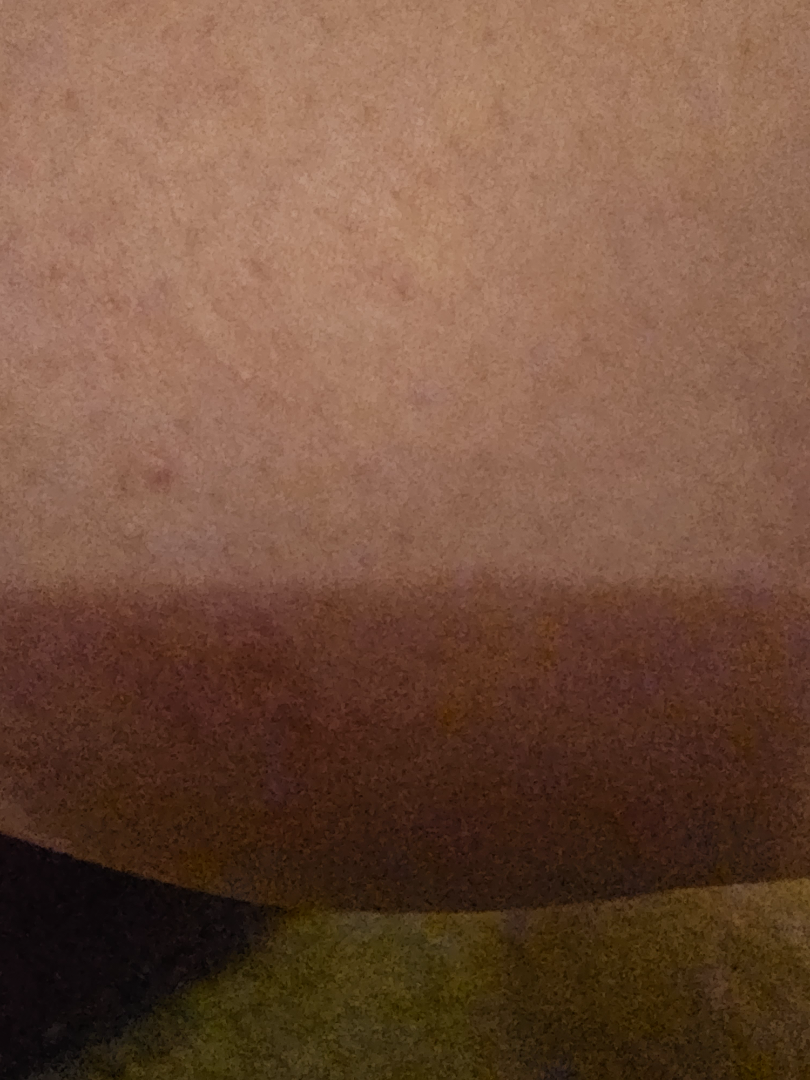Located on the leg. This image was taken at an angle. The condition has been present for three to twelve months. The lesion is associated with bothersome appearance and pain. Non-clinician graders estimated MST 2 (US pool) or 3 (India pool). Texture is reported as fluid-filled and raised or bumpy. The patient considered this a rash. Most consistent with Urticaria.